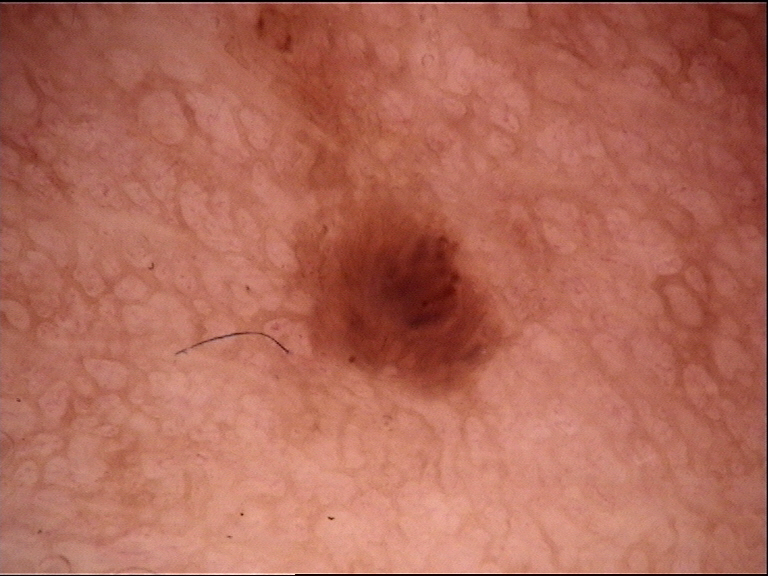modality=dermatoscopy
assessment=compound nevus (expert consensus)